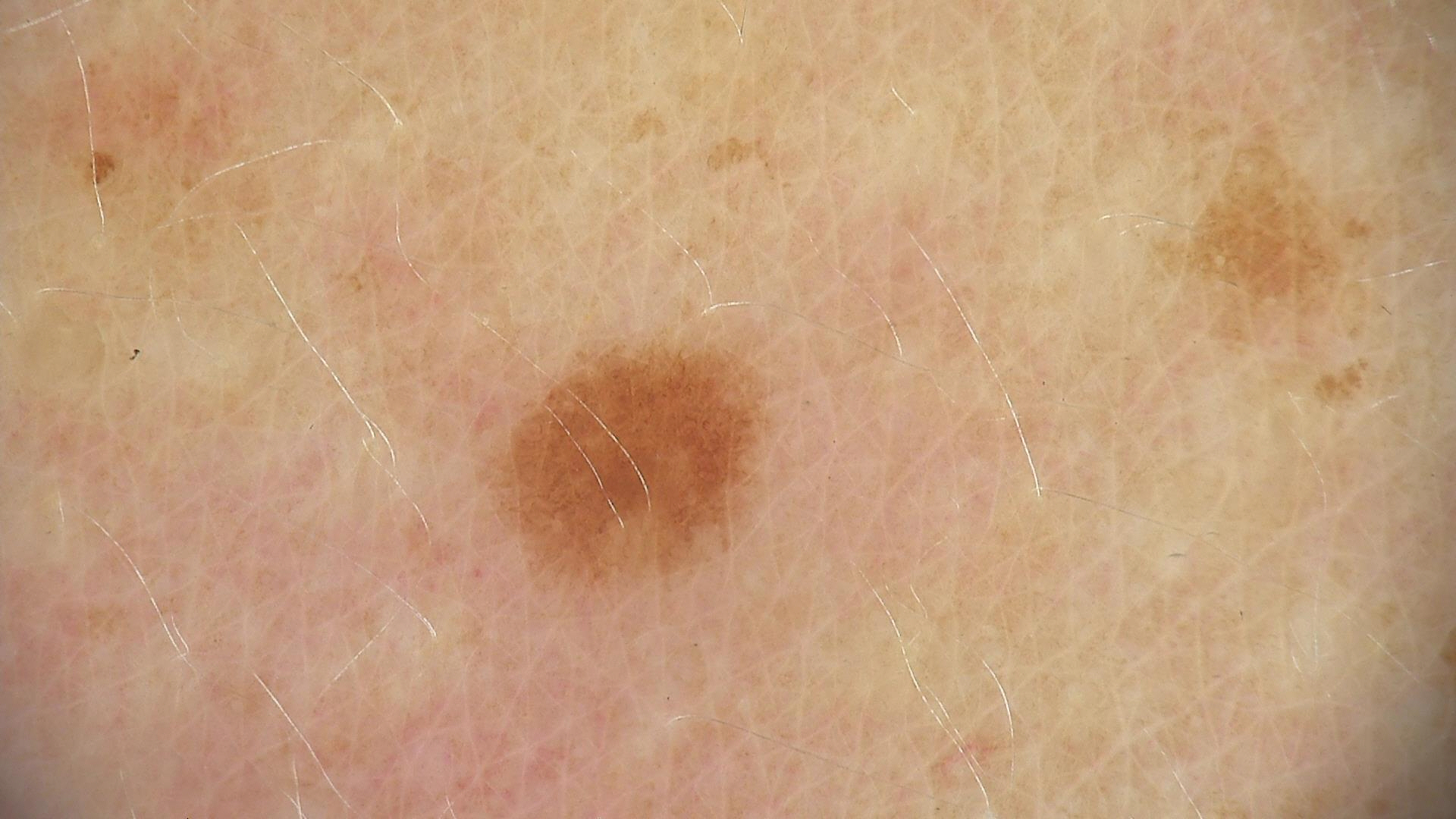Case:
Dermoscopy of a skin lesion.
Conclusion:
Diagnosed as a benign lesion — a dysplastic junctional nevus.